Dermoscopy of a skin lesion.
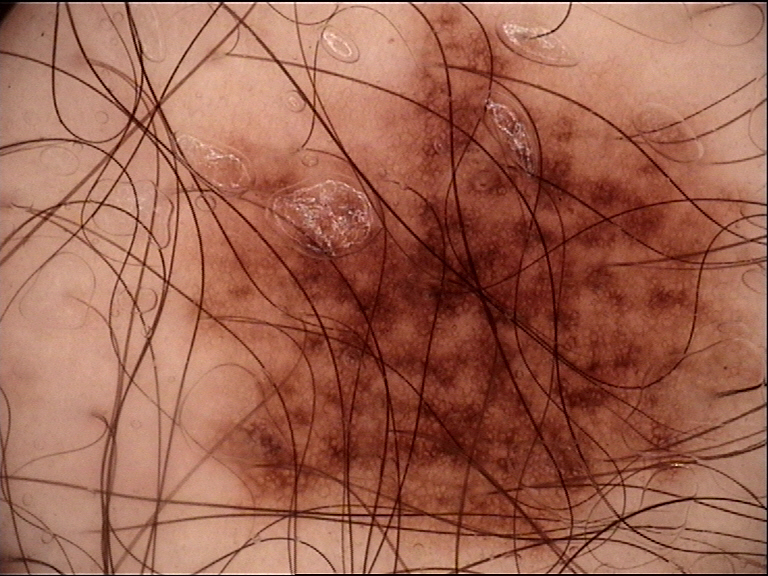The diagnostic label was a dysplastic junctional nevus.